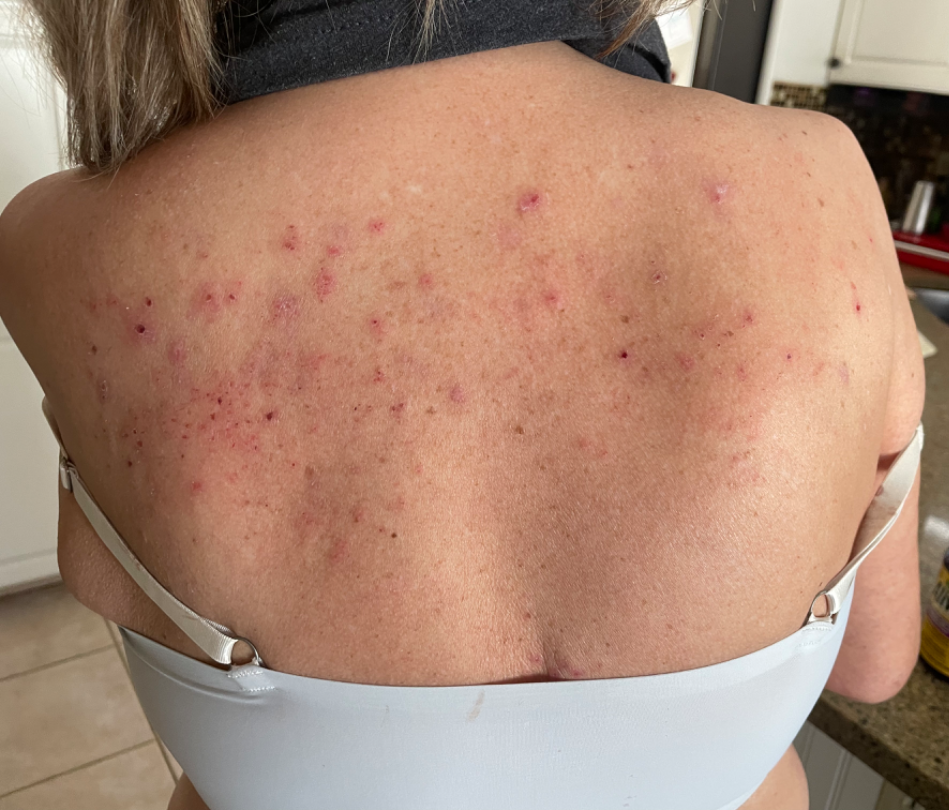view=close-up | affected area=back of the torso | onset=one to four weeks | surface texture=raised or bumpy | clinical impression=Lichen Simplex Chronicus (weight 0.67); Eczema (weight 0.33).